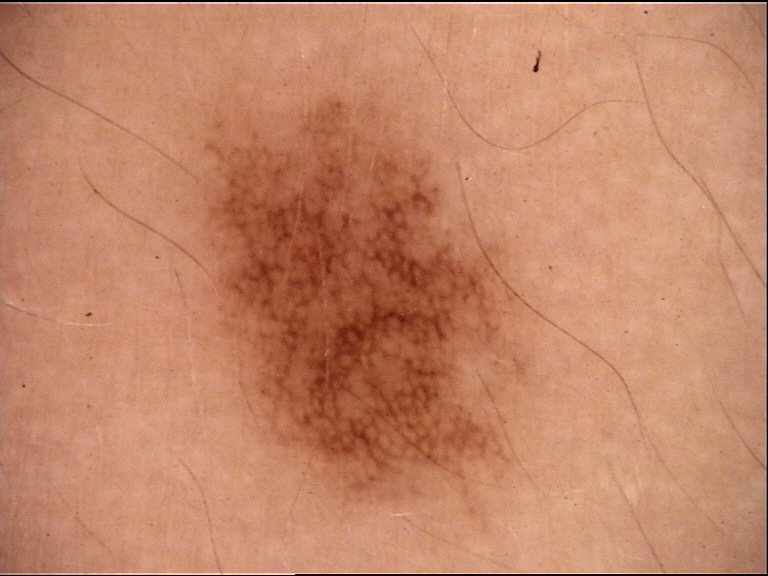| field | value |
|---|---|
| modality | dermatoscopy |
| diagnostic label | dysplastic junctional nevus (expert consensus) |